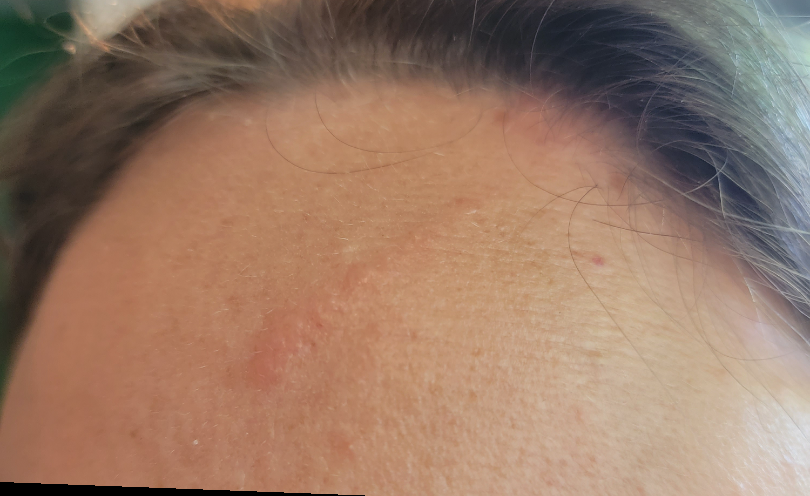The reviewing dermatologist was unable to assign a differential diagnosis from the image. A close-up photograph. The lesion involves the head or neck.